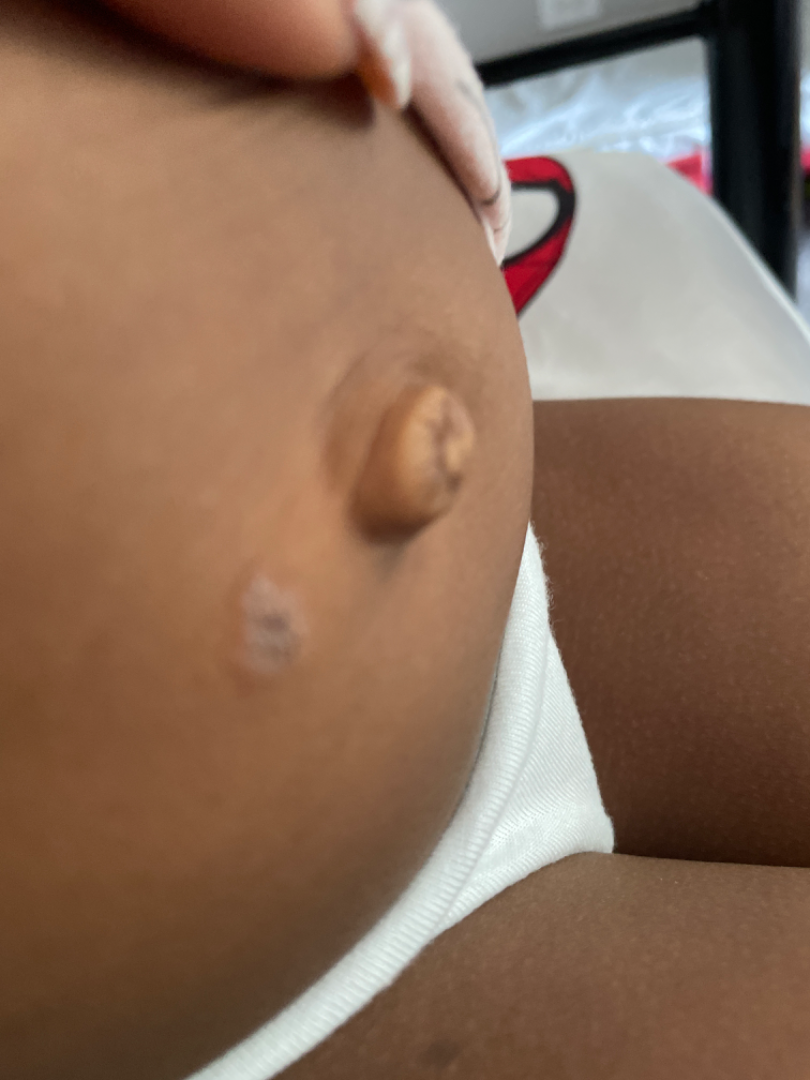• assessment: unable to determine
• lesion texture: raised or bumpy
• framing: at an angle
• patient-reported symptoms: bothersome appearance
• skin tone: Fitzpatrick phototype V
• symptom duration: one to four weeks